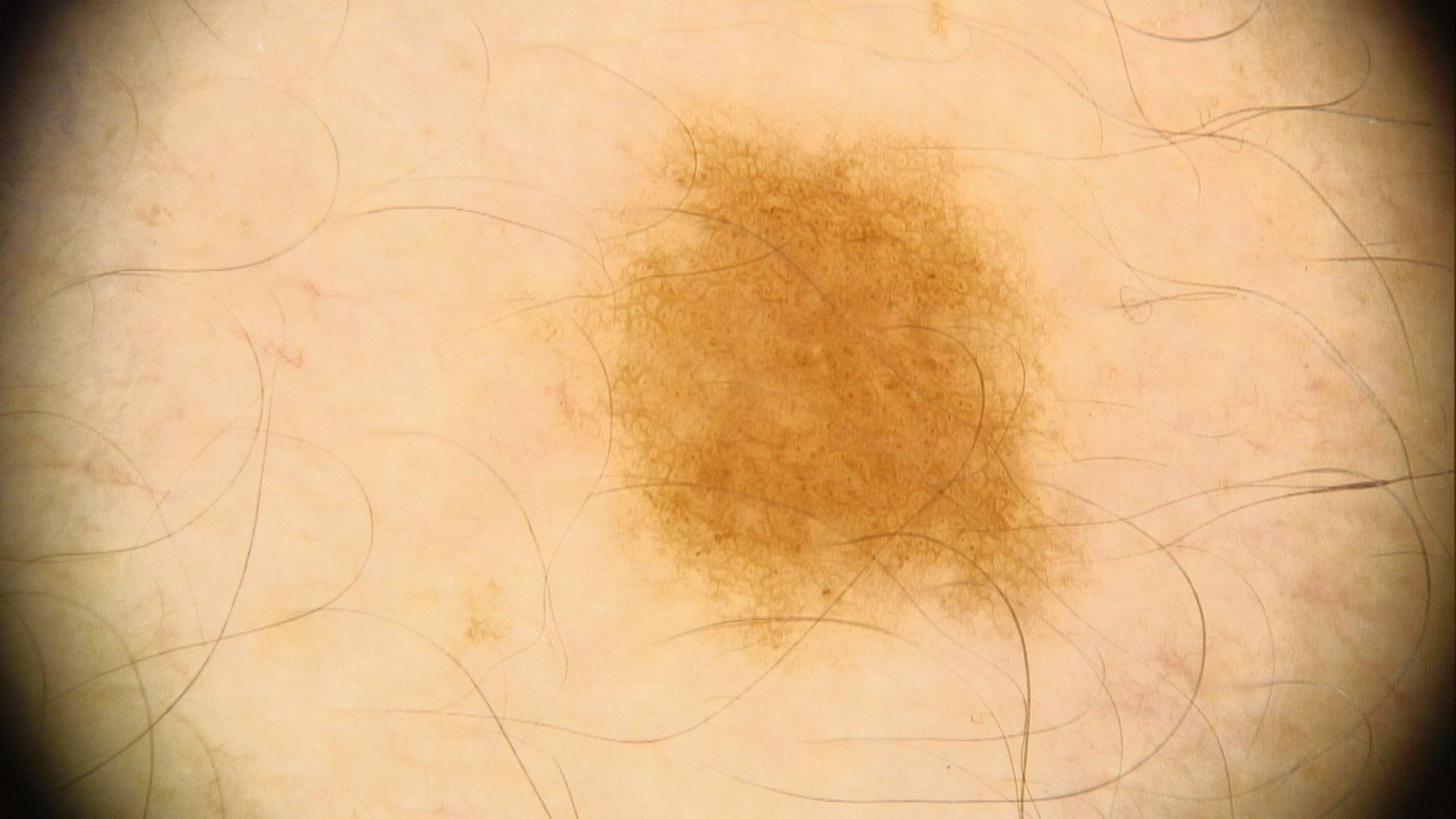Notes:
* patient: female, aged approximately 20
* image type: contact-polarized dermoscopy
* location: an upper extremity
* diagnosis: Nevus (clinical impression)